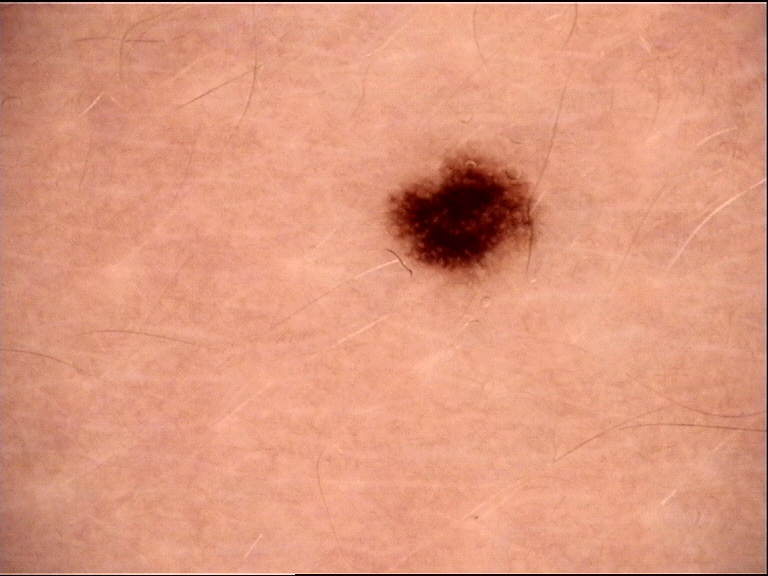Labeled as a junctional nevus.